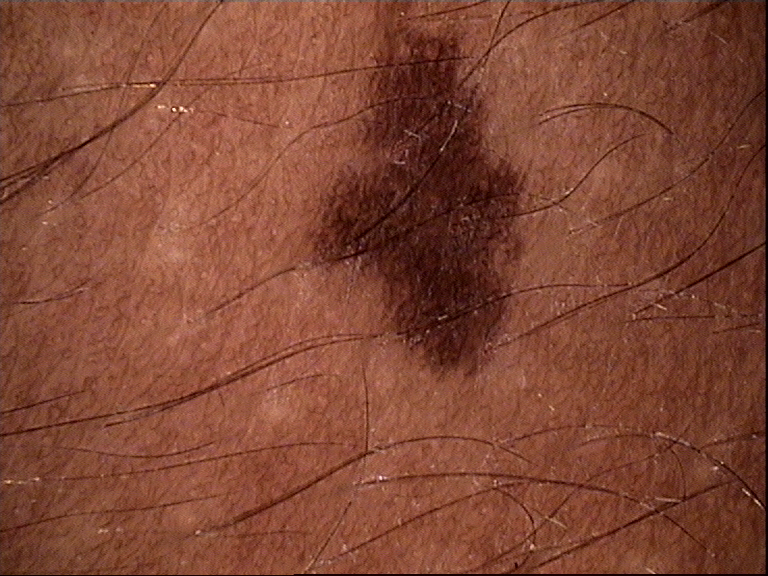Conclusion: Labeled as a dysplastic junctional nevus.